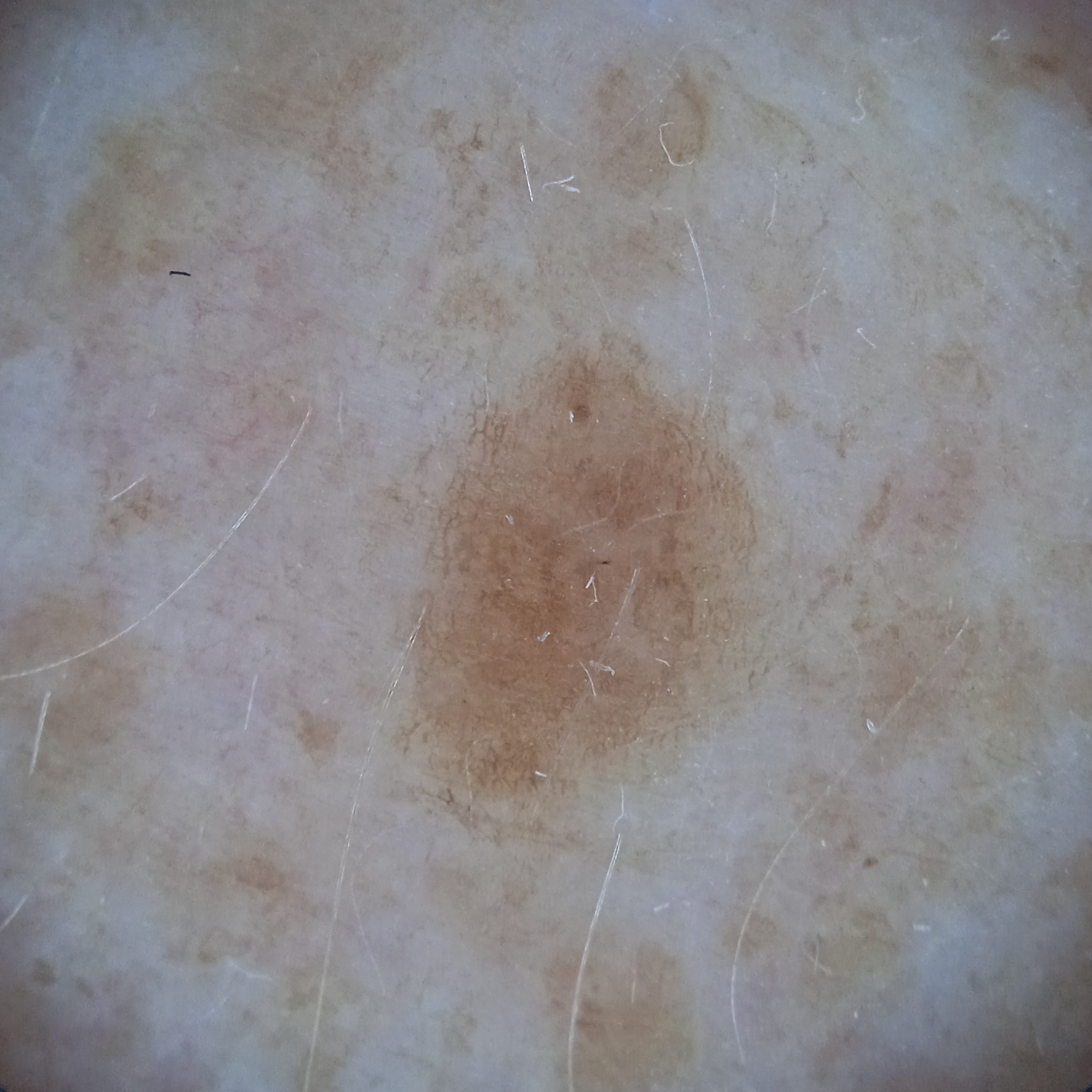Case summary: The patient describes having numerous moles. By self-report, no personal history of cancer and no personal history of skin cancer. The lesion is located on an arm. The lesion is about 5.3 mm across. Conclusion: On independent review by four dermatologists, the agreed diagnosis was a seborrheic keratosis; diagnostic confidence was good; also considered: a melanocytic nevus.